A clinical close-up photograph of a skin lesion.
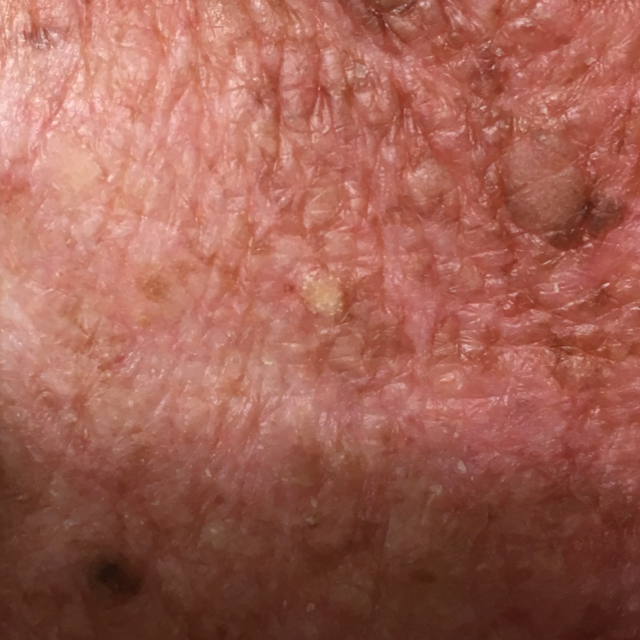Clinical context: The patient reports that the lesion itches. Conclusion: Consistent with an actinic keratosis.